A dermoscopic image of a skin lesion; a moderate number of moles by the patient's own estimate; the patient says their skin reddens with sun exposure; a female patient age 59:
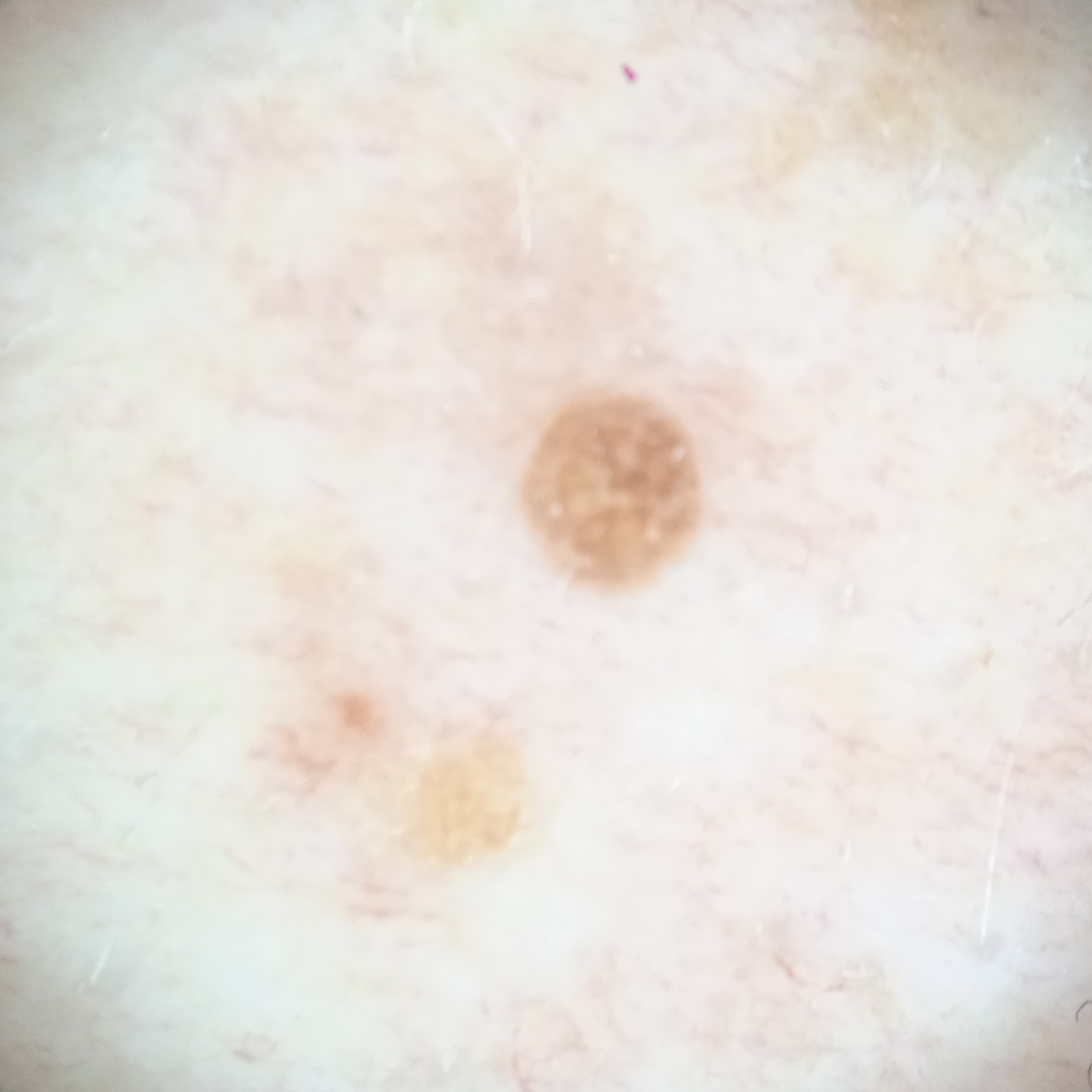Q: Where is the lesion?
A: the torso
Q: What was the diagnosis?
A: seborrheic keratosis (dermatologist consensus)